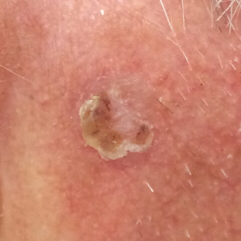The patient was assessed as FST II.
A clinical close-up photograph of a skin lesion.
The chart notes prior skin cancer (patient or family).
The lesion is roughly 6 by 6 mm.
Biopsy-confirmed as a malignancy — a basal cell carcinoma.